A skin lesion imaged with a dermatoscope. A female subject about 40 years old.
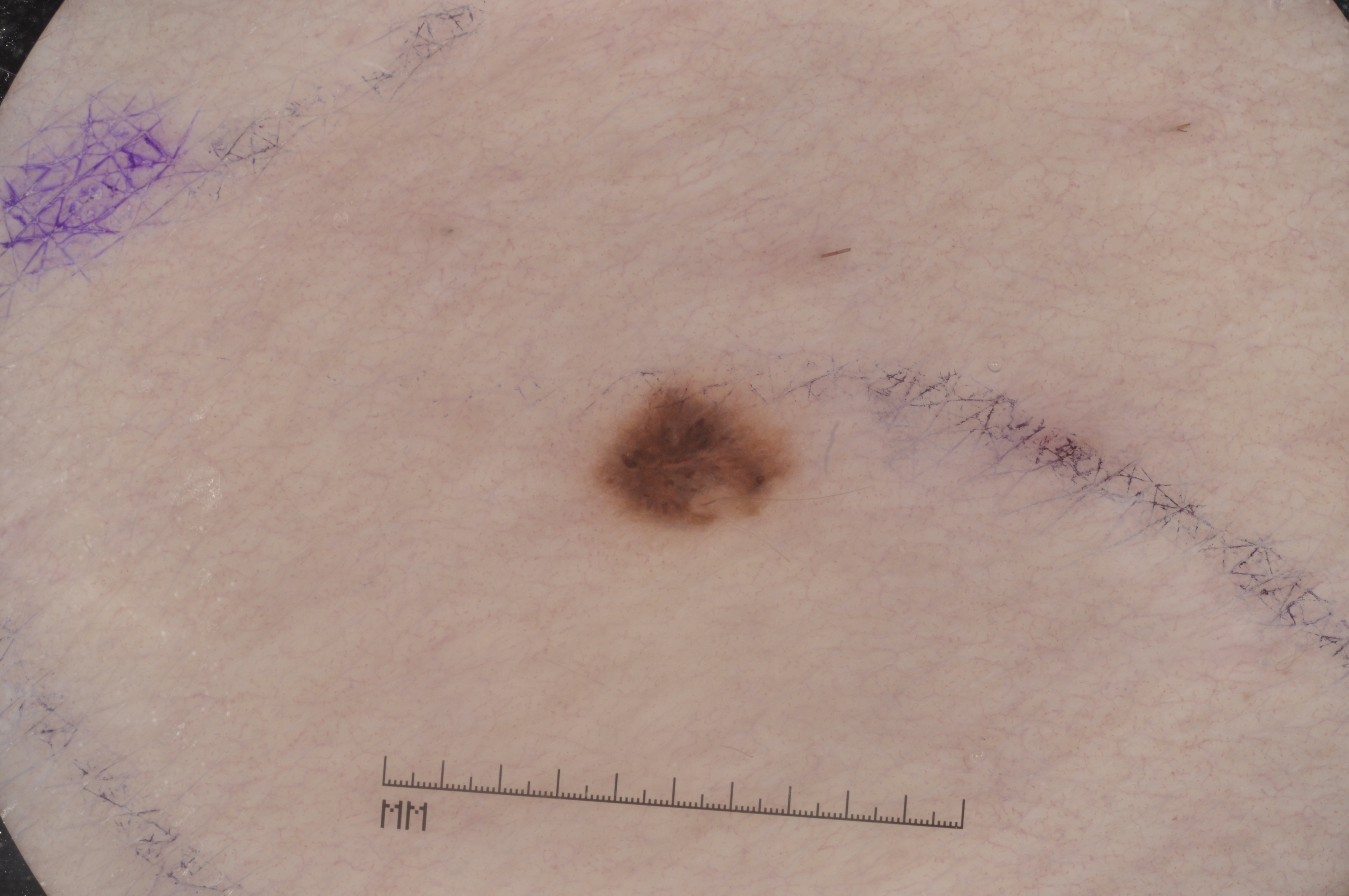{
  "lesion_extent": "small",
  "dermoscopic_features": {
    "present": [],
    "absent": [
      "milia-like cysts",
      "pigment network",
      "streaks",
      "negative network"
    ]
  },
  "lesion_location": {
    "bbox_xyxy": [
      580,
      371,
      801,
      539
    ]
  },
  "diagnosis": {
    "name": "melanocytic nevus",
    "malignancy": "benign",
    "lineage": "melanocytic",
    "provenance": "clinical"
  }
}